A dermoscopy image of a single skin lesion:
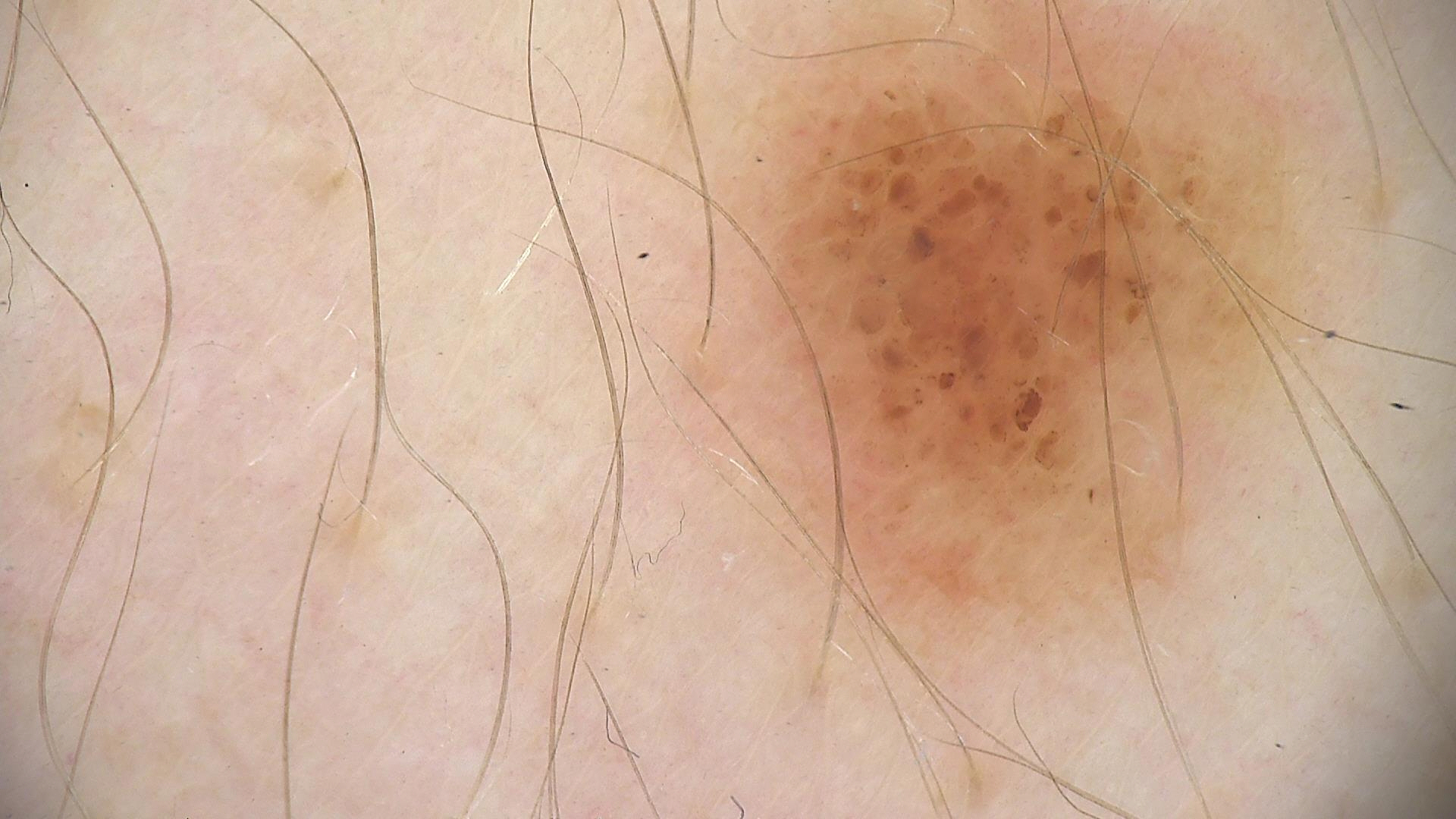Findings:
- lesion type — banal
- diagnostic label — compound nevus (expert consensus)